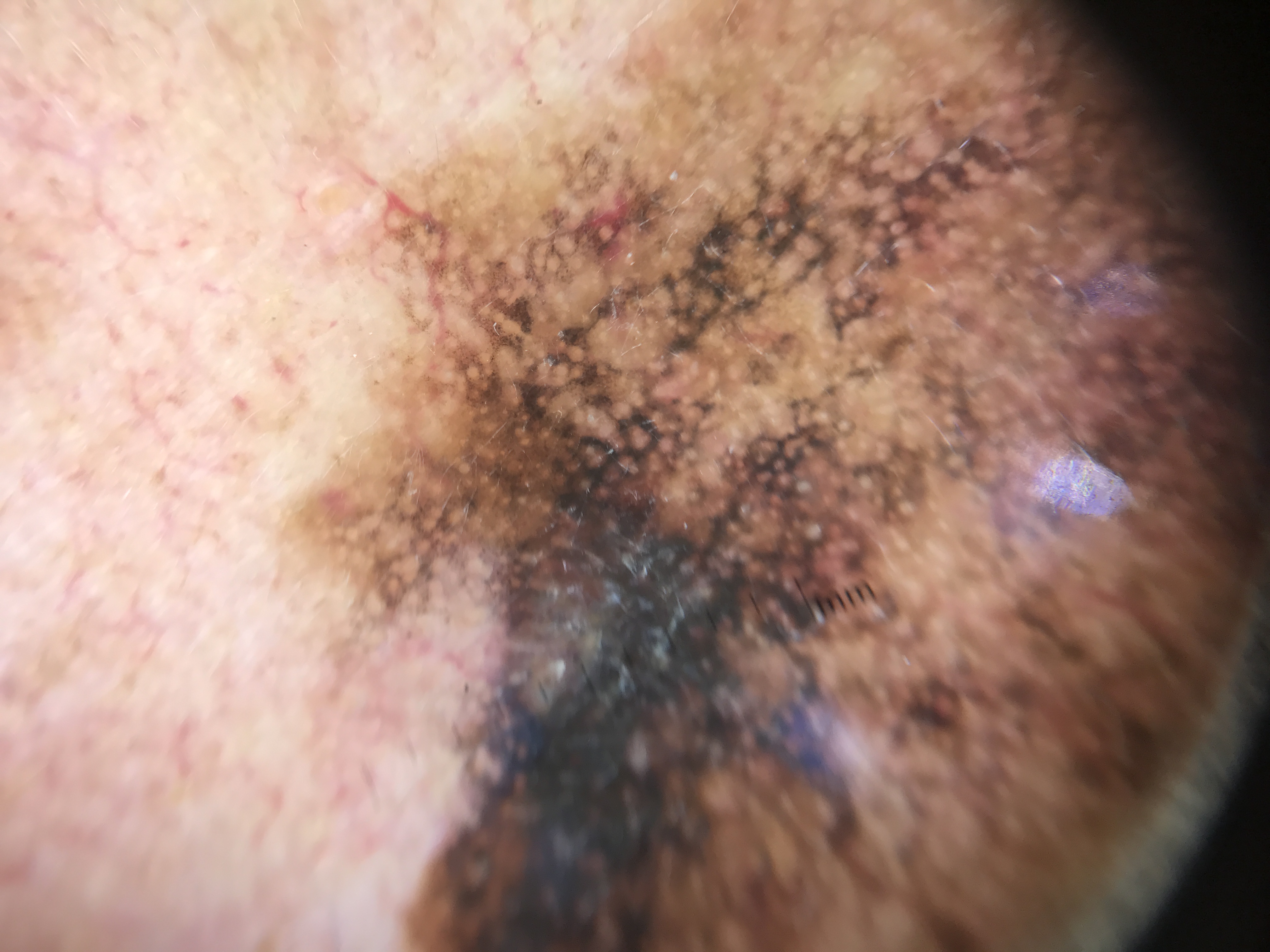label = lentigo maligna (biopsy-proven).